A female subject roughly 50 years of age — 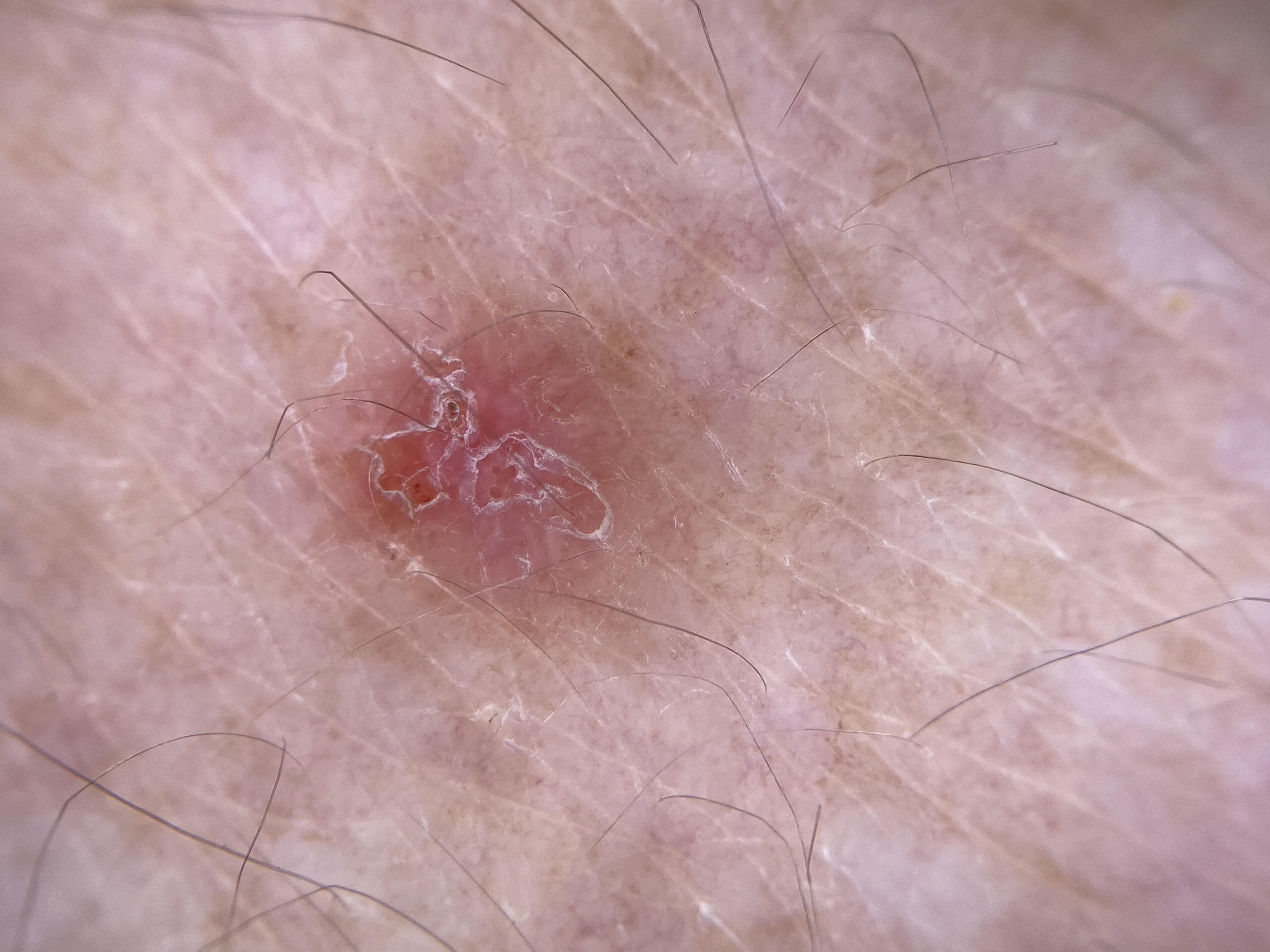{
  "lesion_location": {
    "region": "a lower extremity"
  },
  "diagnosis": {
    "name": "Basal cell carcinoma",
    "malignancy": "malignant",
    "confirmation": "histopathology",
    "lineage": "adnexal"
  }
}